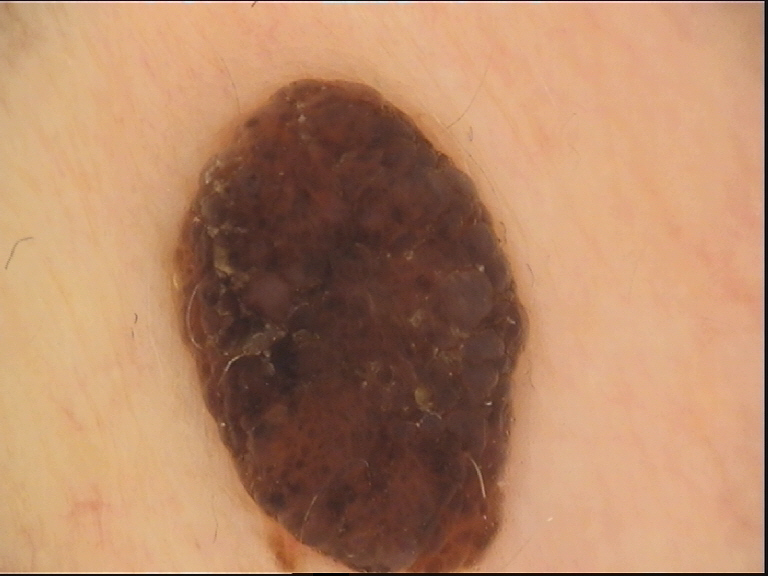A skin lesion imaged with a dermatoscope.
Labeled as a dermal nevus.